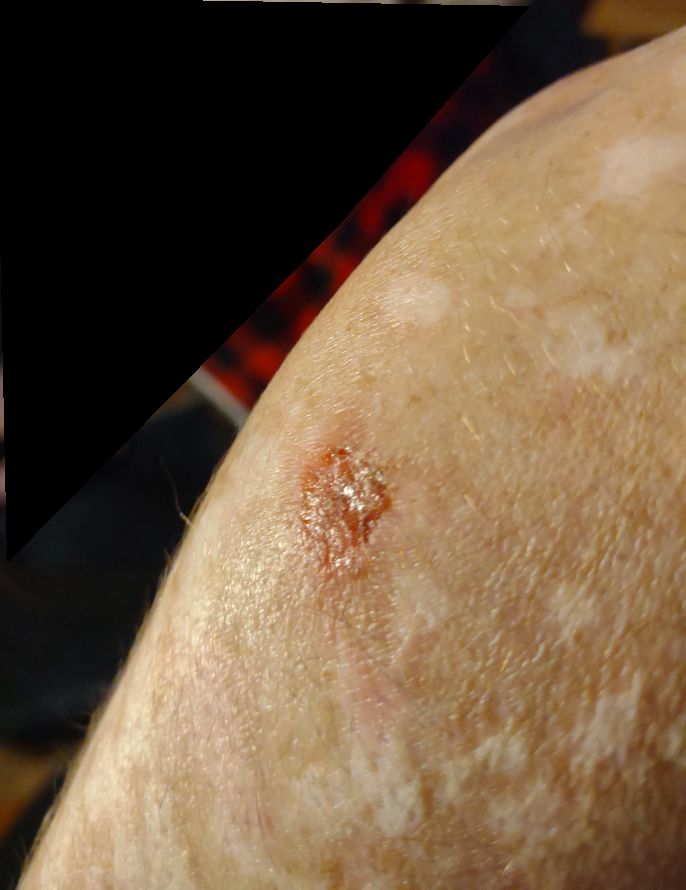The leading impression is Impetigo; with consideration of Inflicted skin lesions; the differential also includes Bullous Pemphigoid; less probable is Skin cancer.